A subject age 67 · a clinical photograph showing a skin lesion:
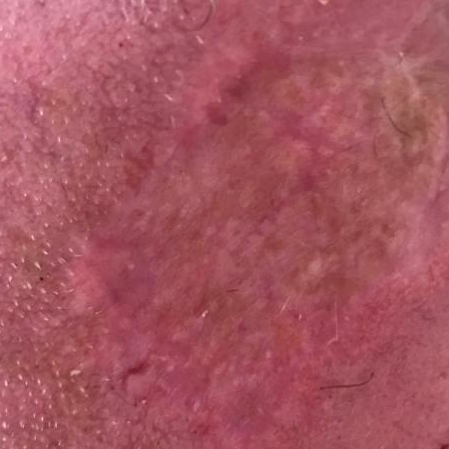The lesion is on the face.
Diagnosed by dermatologist consensus as an actinic keratosis.